A dermoscopic close-up of a skin lesion.
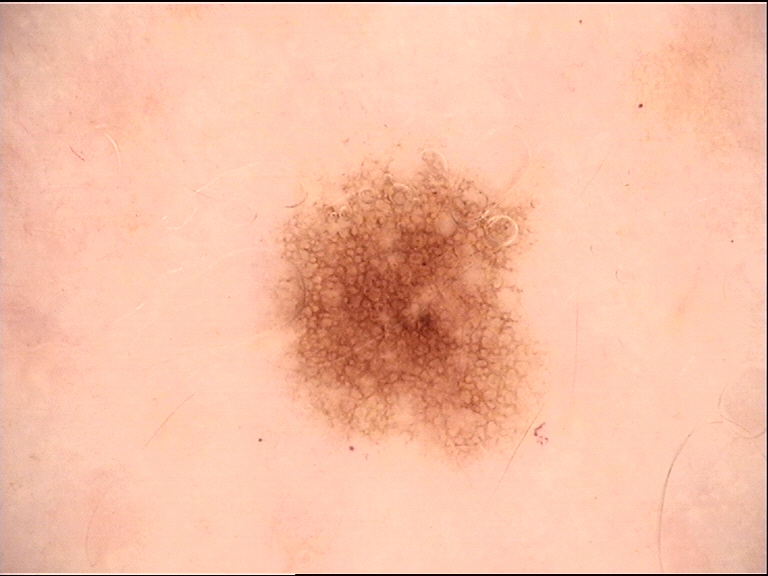class — dysplastic junctional nevus (expert consensus).